An image taken at a distance. The contributor is 30–39, female. The front of the torso is involved.
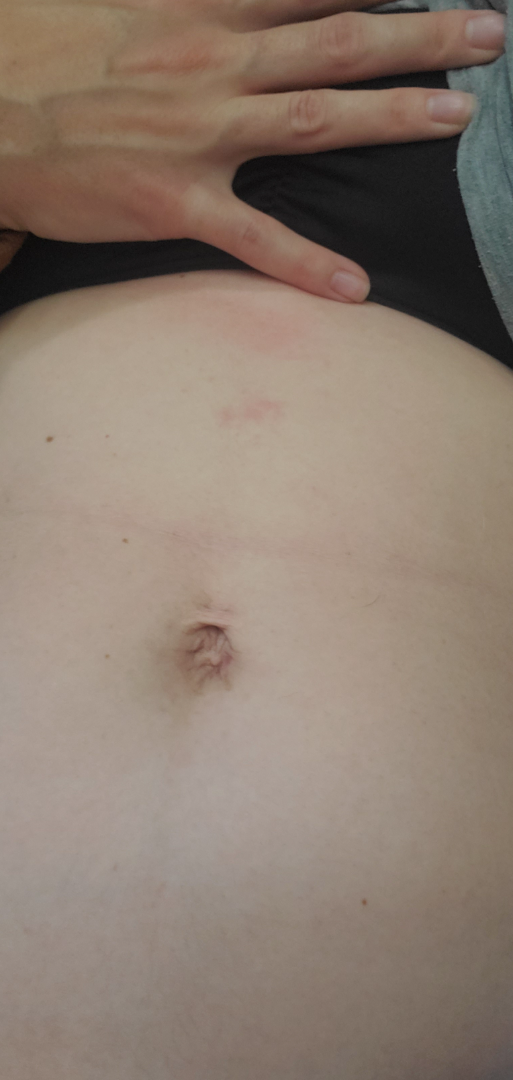{
  "assessment": "could not be assessed",
  "patient_category": "a rash",
  "symptoms": "itching",
  "duration": "about one day",
  "texture": "raised or bumpy"
}